A dermoscopic close-up of a skin lesion: 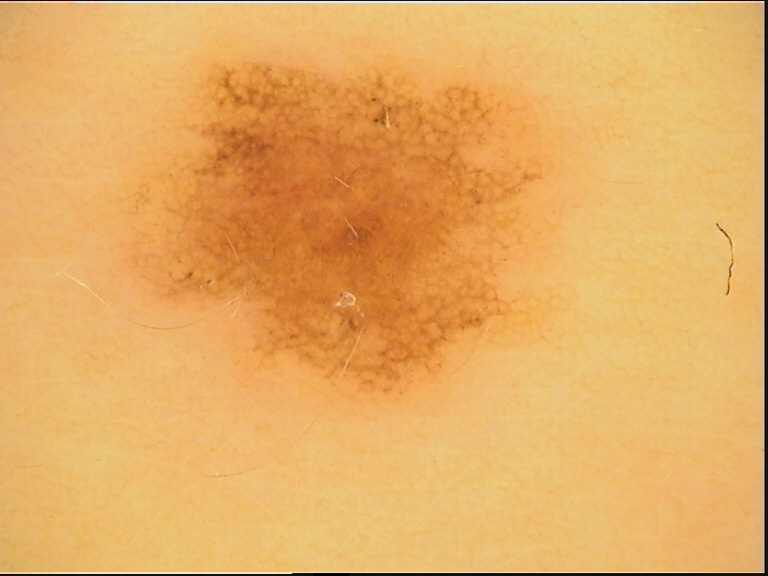The diagnosis was a benign lesion — a dysplastic junctional nevus.